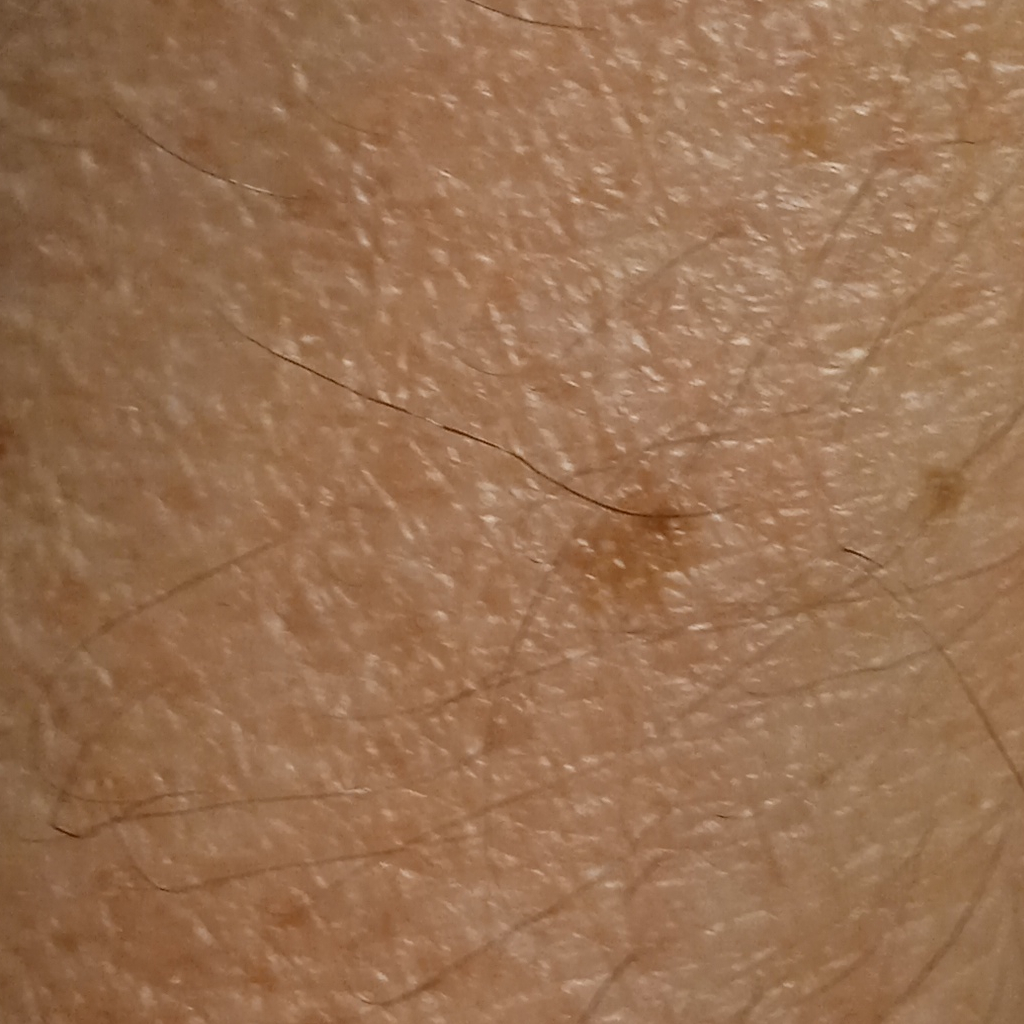A male subject 79 years of age. A clinical close-up of a skin lesion. Collected as part of a research study, without a referral diagnosis. The lesion involves an arm. Measuring roughly 4.2 mm. The diagnostic impression was a seborrheic keratosis.